Dermoscopy of a skin lesion: 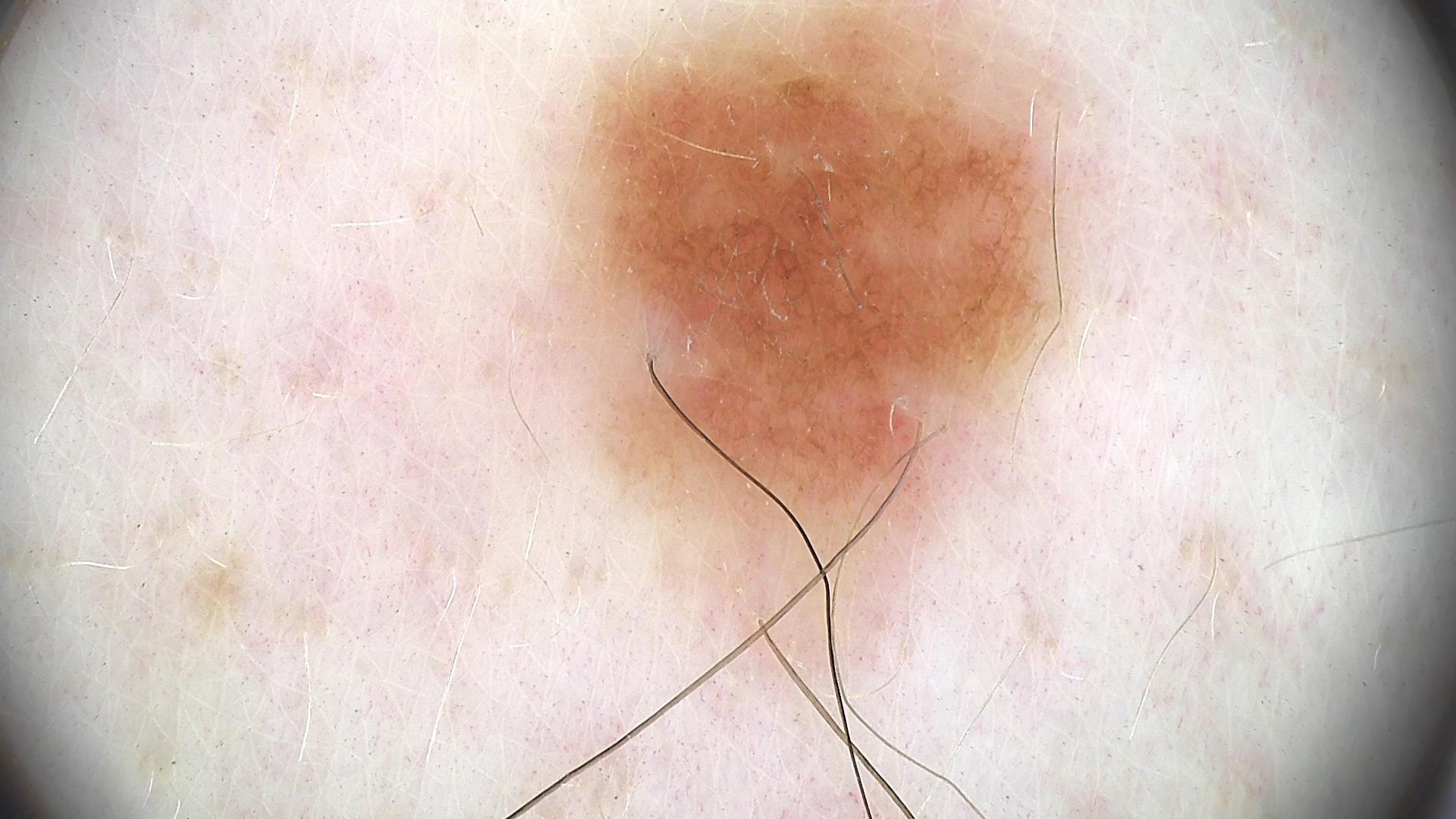Diagnosed as a dysplastic junctional nevus.